A clinical photograph showing a skin lesion · a female subject 39 years of age · imaged for a research study, with no referral diagnosis recorded.
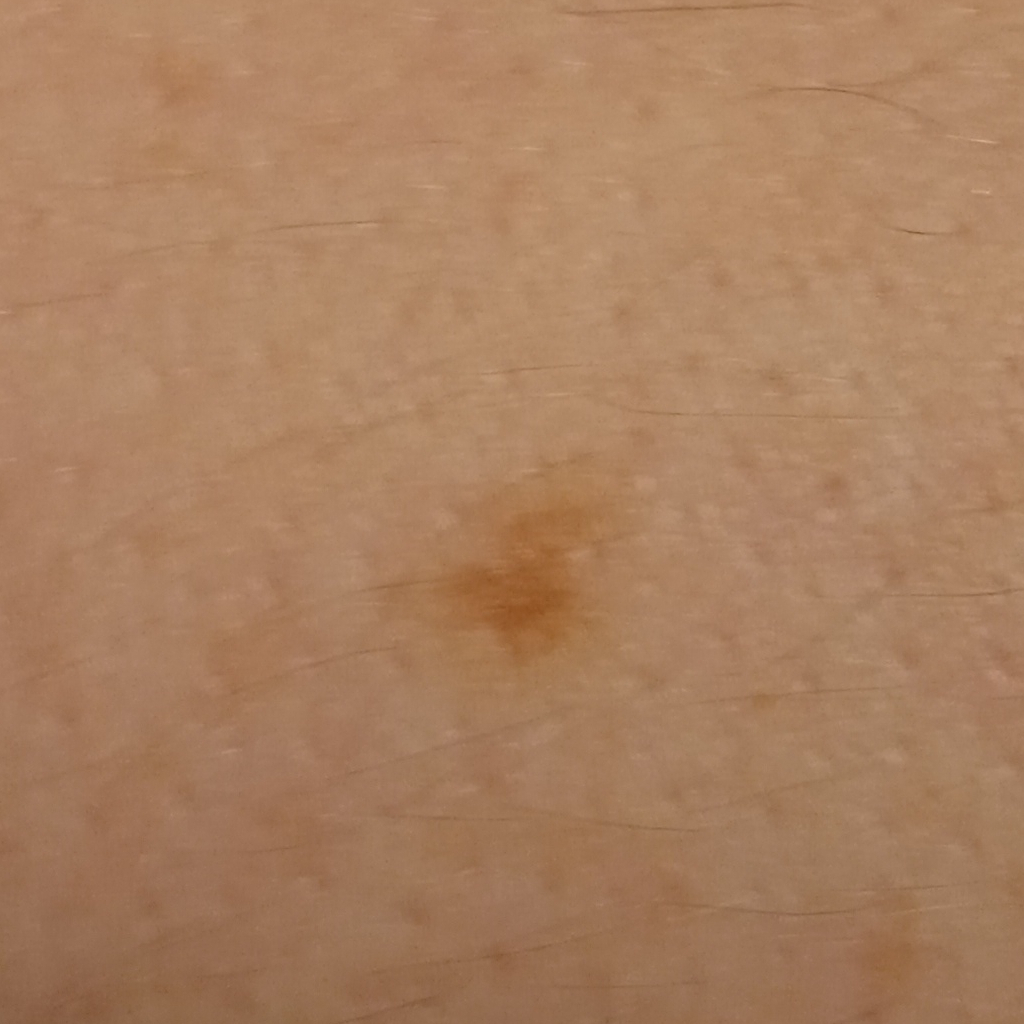Clinical context:
The lesion is on an arm. The lesion measures approximately 5.1 mm.
Conclusion:
Dermatologist review favored a melanocytic nevus.